A dermoscopic photograph of a skin lesion:
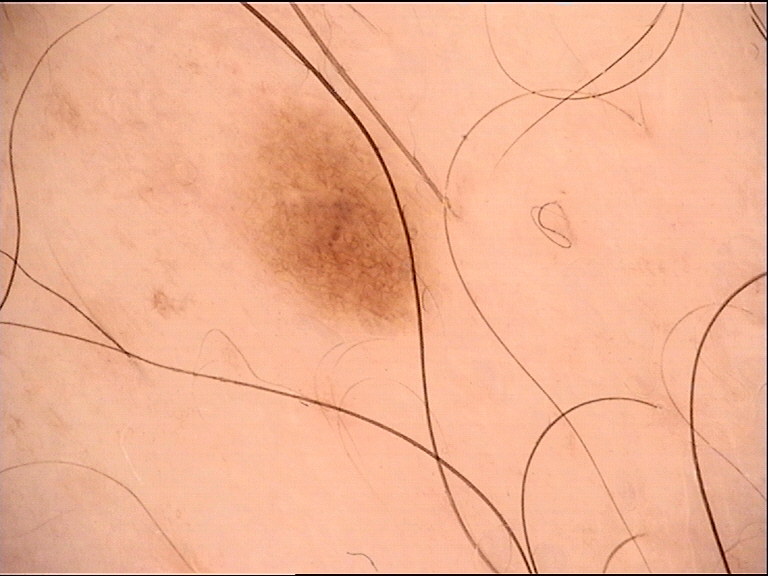Findings:
- label: dysplastic junctional nevus (expert consensus)